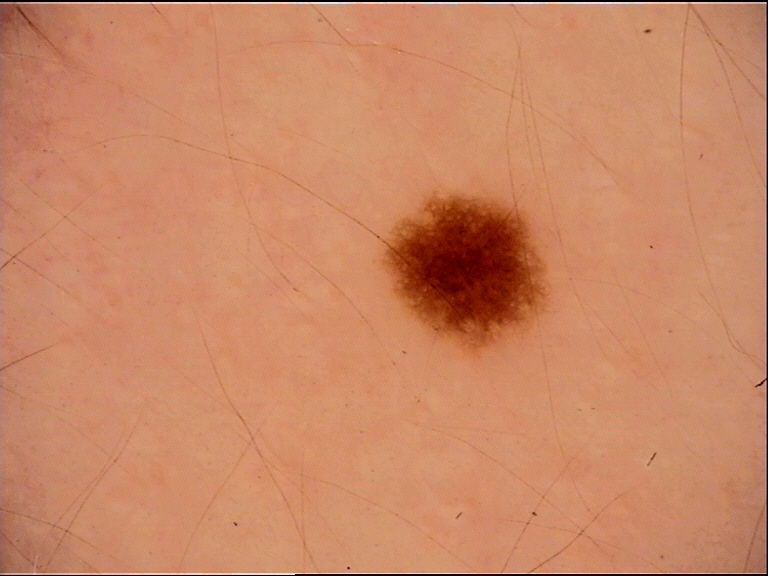Consistent with a dysplastic junctional nevus.